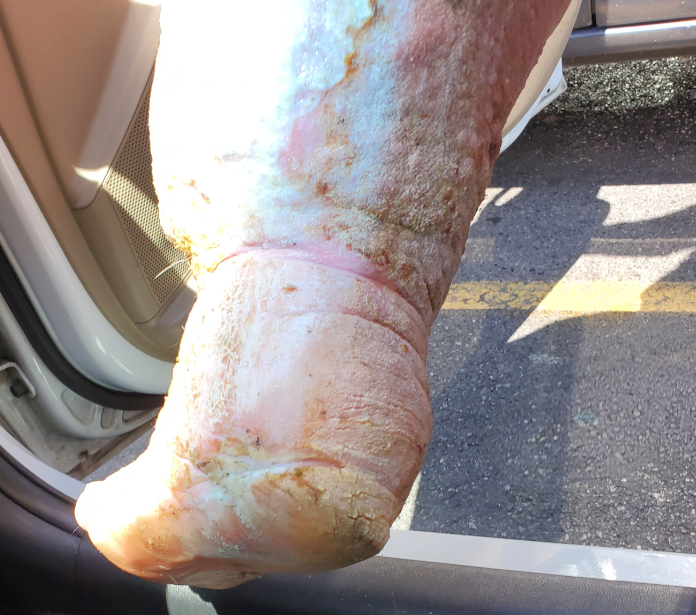The skin findings could not be characterized from the image. A close-up photograph.